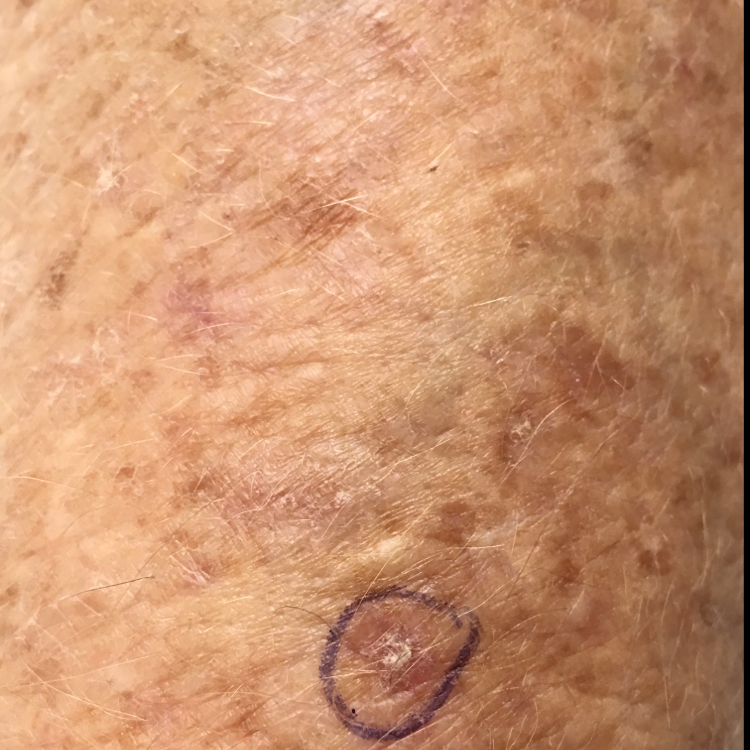Diagnosed by dermatologist consensus as an actinic keratosis.